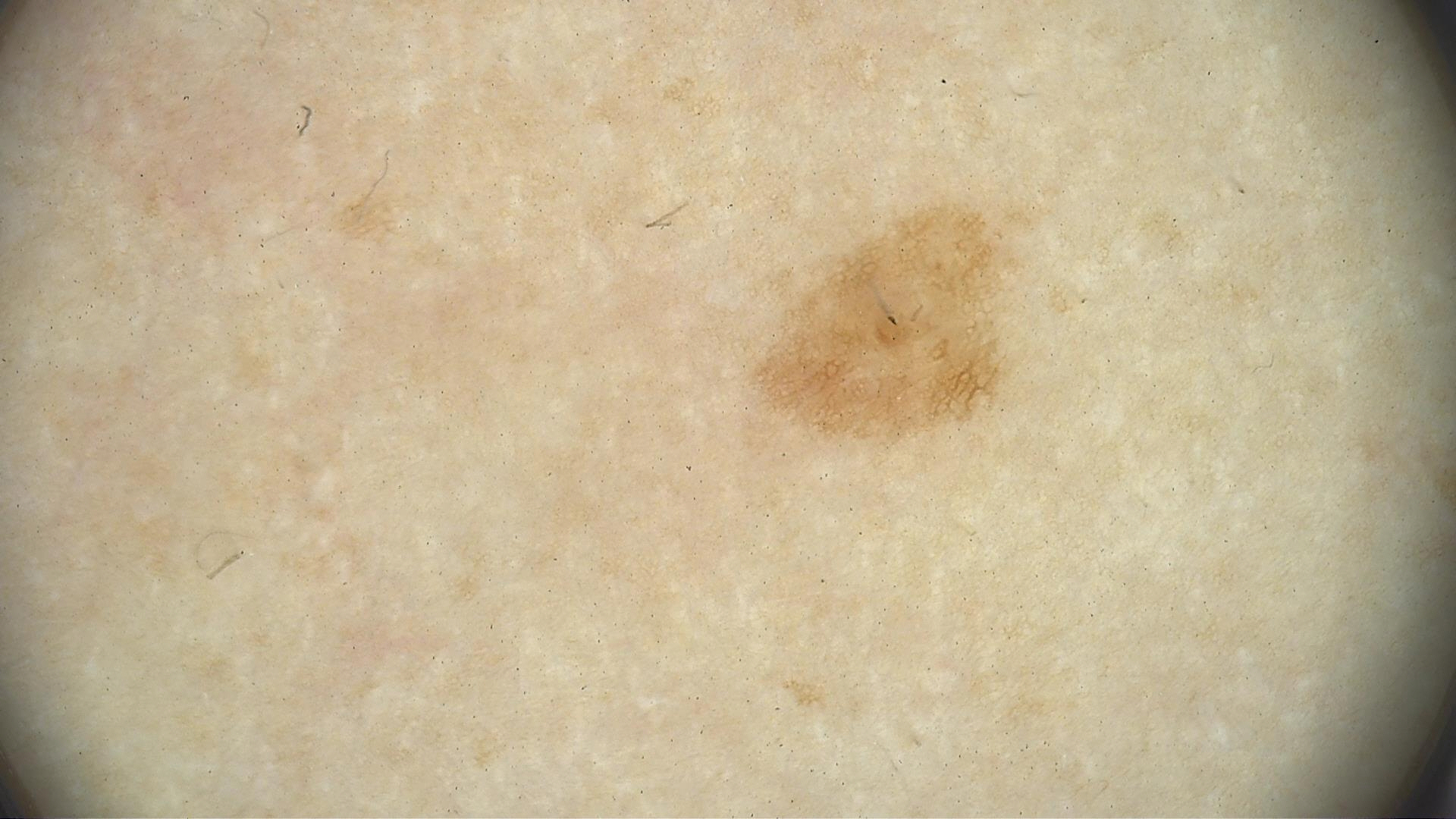Q: What is the imaging modality?
A: dermoscopy
Q: How is the lesion classified?
A: banal
Q: What is the diagnosis?
A: junctional nevus (expert consensus)